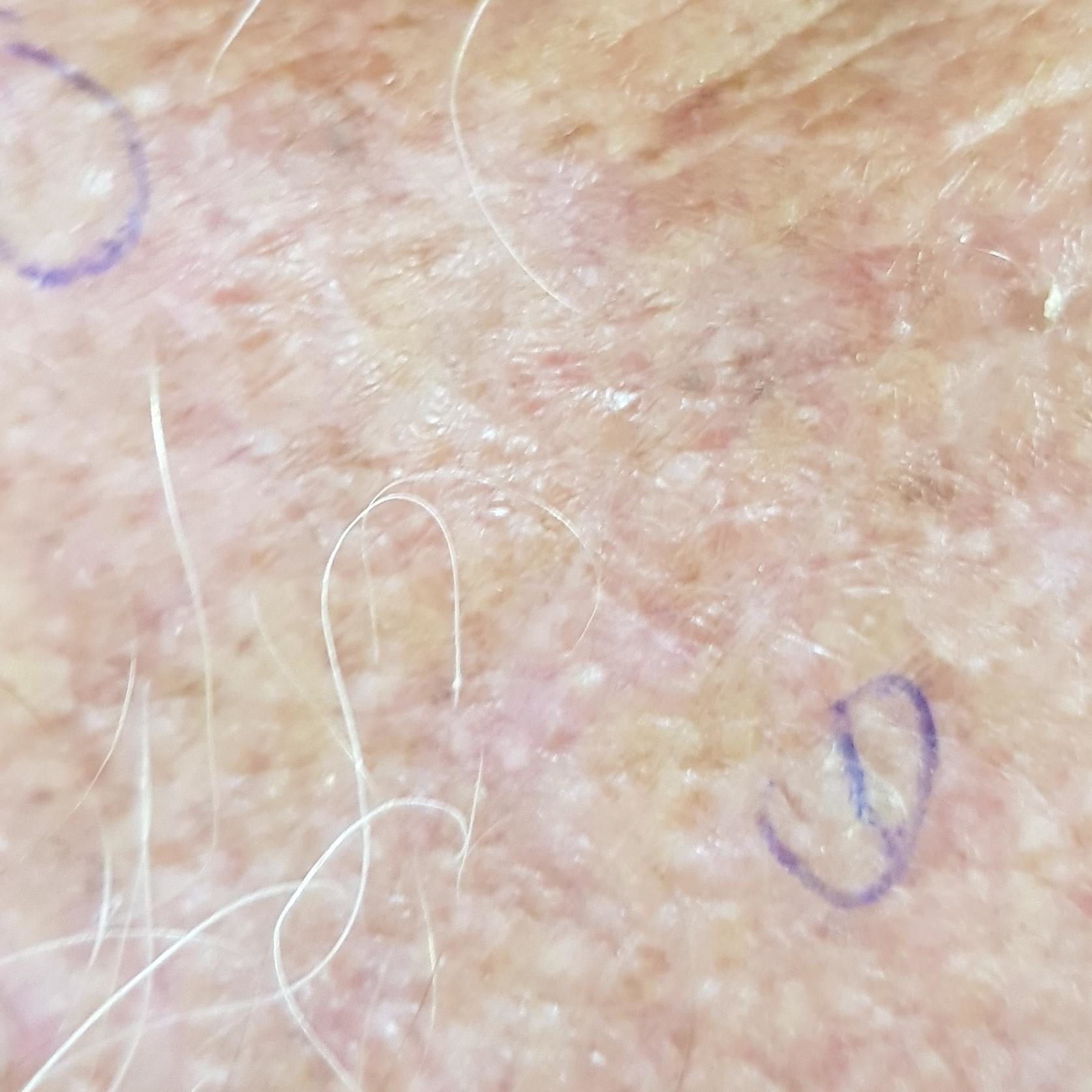Diagnosed by dermatologist consensus as an actinic keratosis.